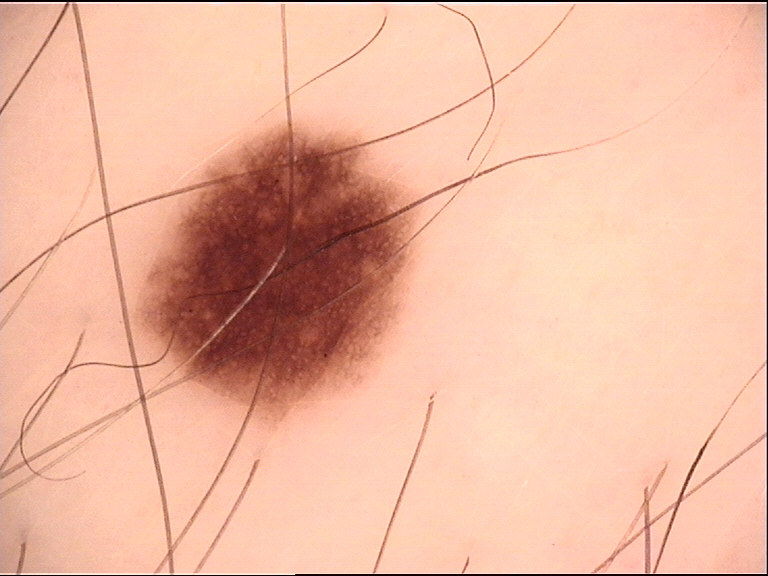diagnostic label=dysplastic junctional nevus (expert consensus).